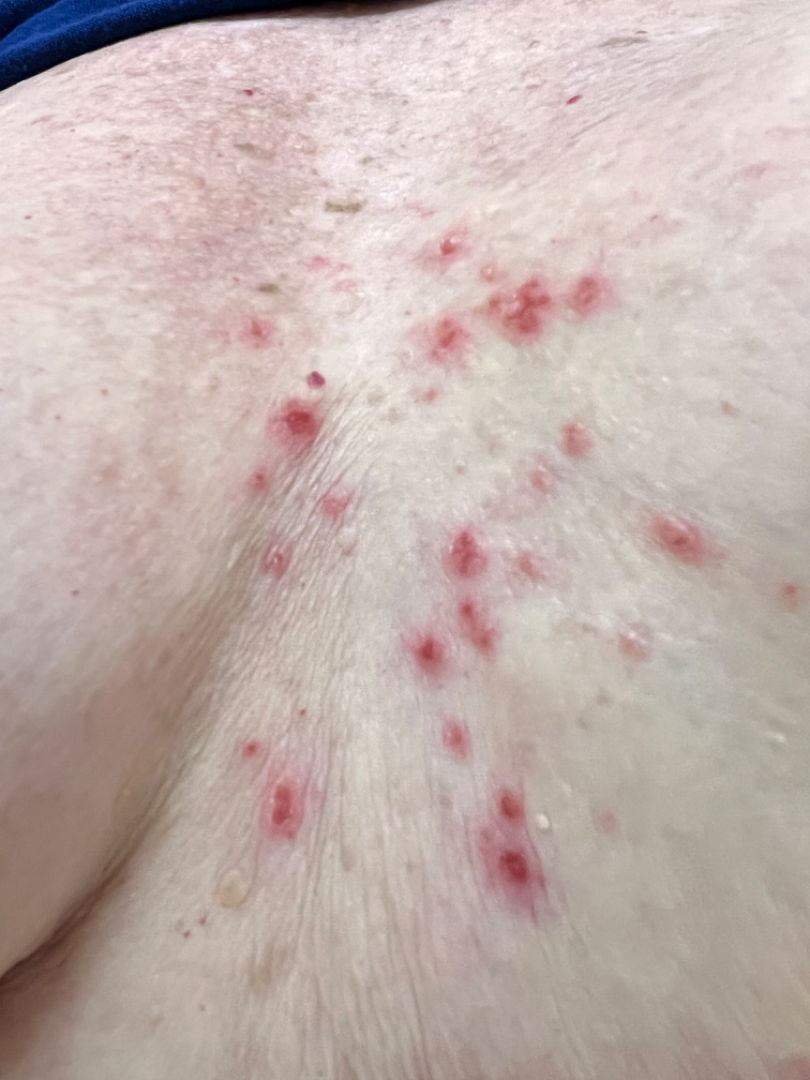| feature | finding |
|---|---|
| differential diagnosis | most consistent with Grover's disease; also consider Folliculitis; a more distant consideration is Acne; less probable is Irritant Contact Dermatitis; less likely is Pemphigus foliaceus; a remote consideration is Seborrheic Dermatitis |